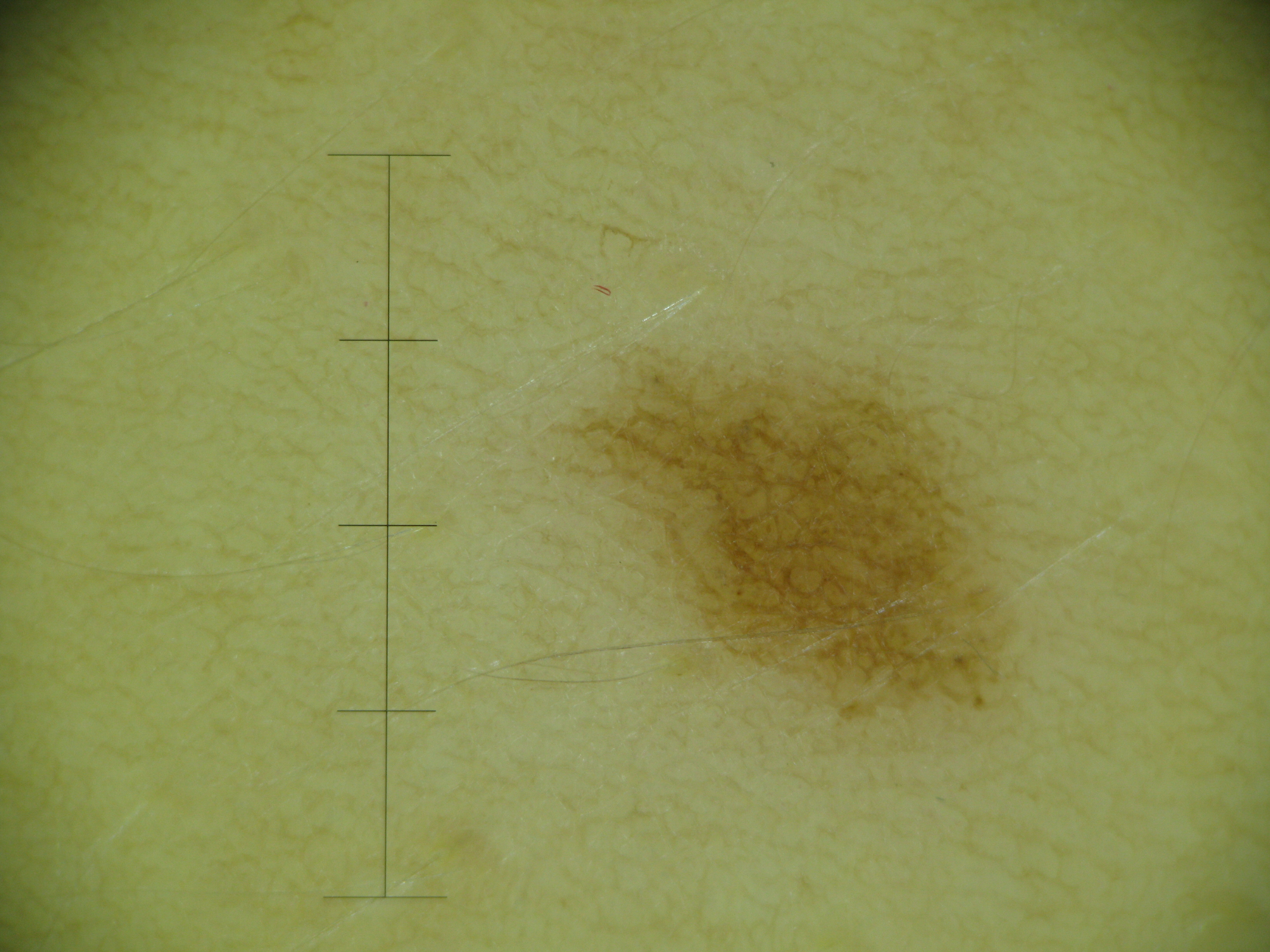A dermoscopic image of a skin lesion.
The morphology is that of a banal lesion.
Diagnosed as a junctional nevus.